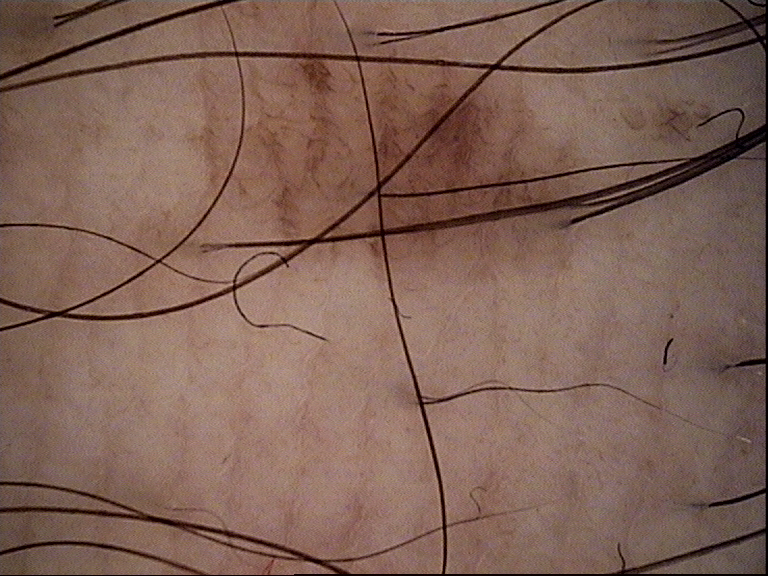image type = dermoscopy, diagnostic label = acral dysplastic junctional nevus (expert consensus).